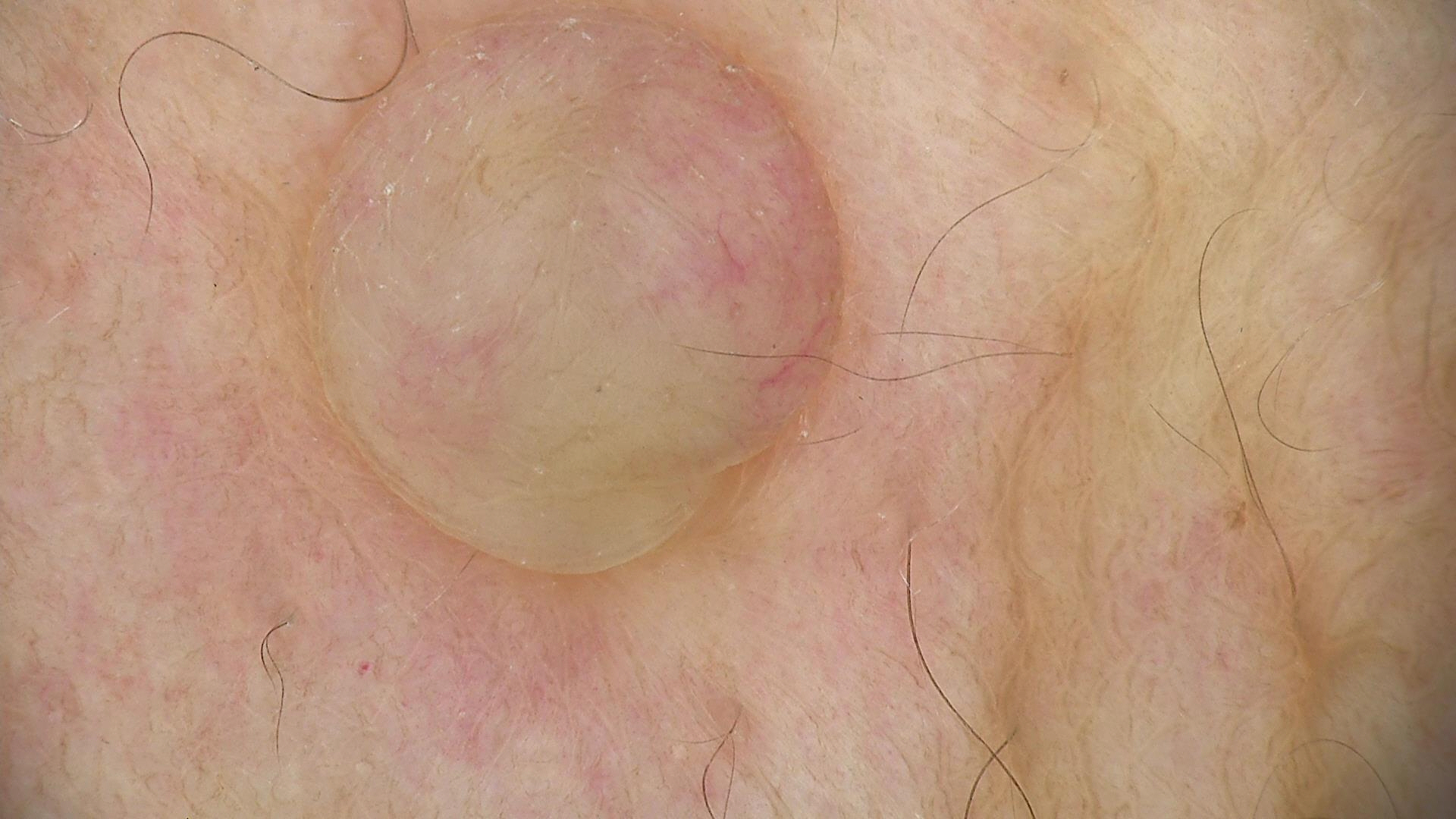<dermoscopy>
<image>dermoscopy</image>
<diagnosis>
<name>dermal nevus</name>
<code>db</code>
<malignancy>benign</malignancy>
<super_class>melanocytic</super_class>
<confirmation>expert consensus</confirmation>
</diagnosis>
</dermoscopy>